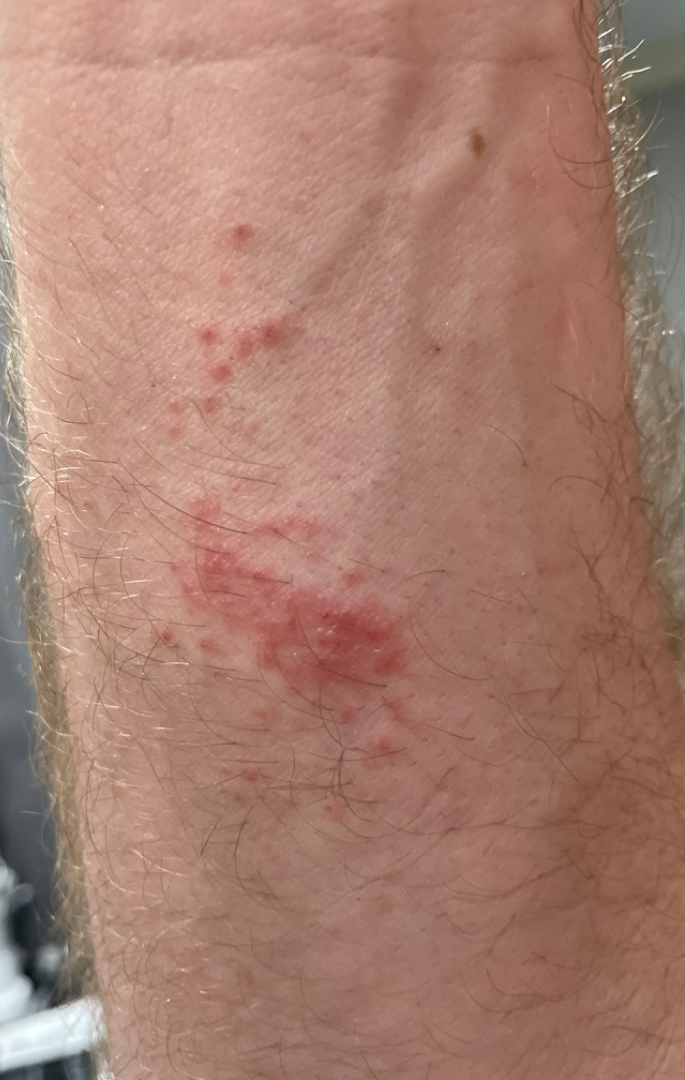Assessment: The skin findings could not be characterized from the image. Clinical context: The condition has been present for less than one week. The patient indicates itching. An image taken at an angle. Male subject, age 40–49. The affected area is the arm.